This is a close-up image; the subject is a female aged 18–29.
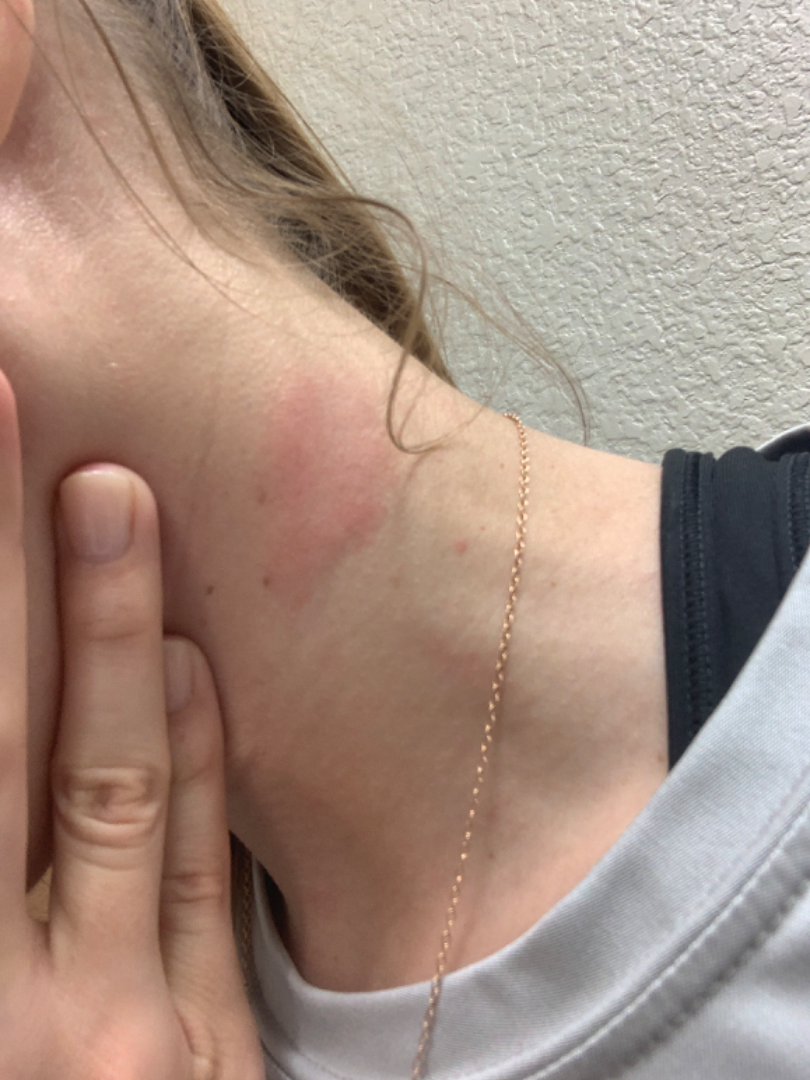Case summary:
– assessment — Urticaria (possible); Allergic Contact Dermatitis (possible)